A skin lesion imaged with a dermatoscope.
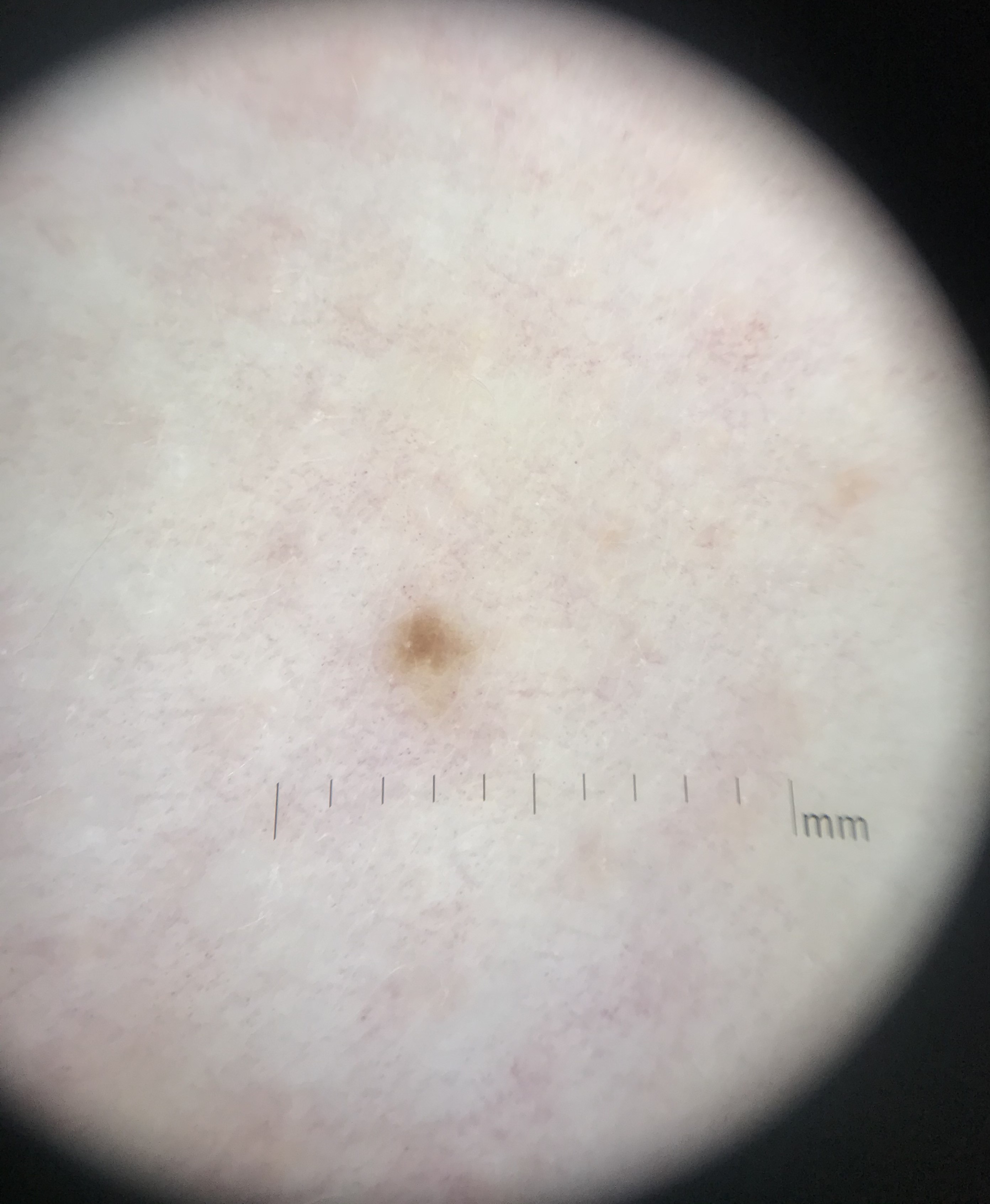The architecture is that of a keratinocytic lesion.
Labeled as a seborrheic keratosis.